The patient is a male roughly 25 years of age · this is a dermoscopic photograph of a skin lesion.
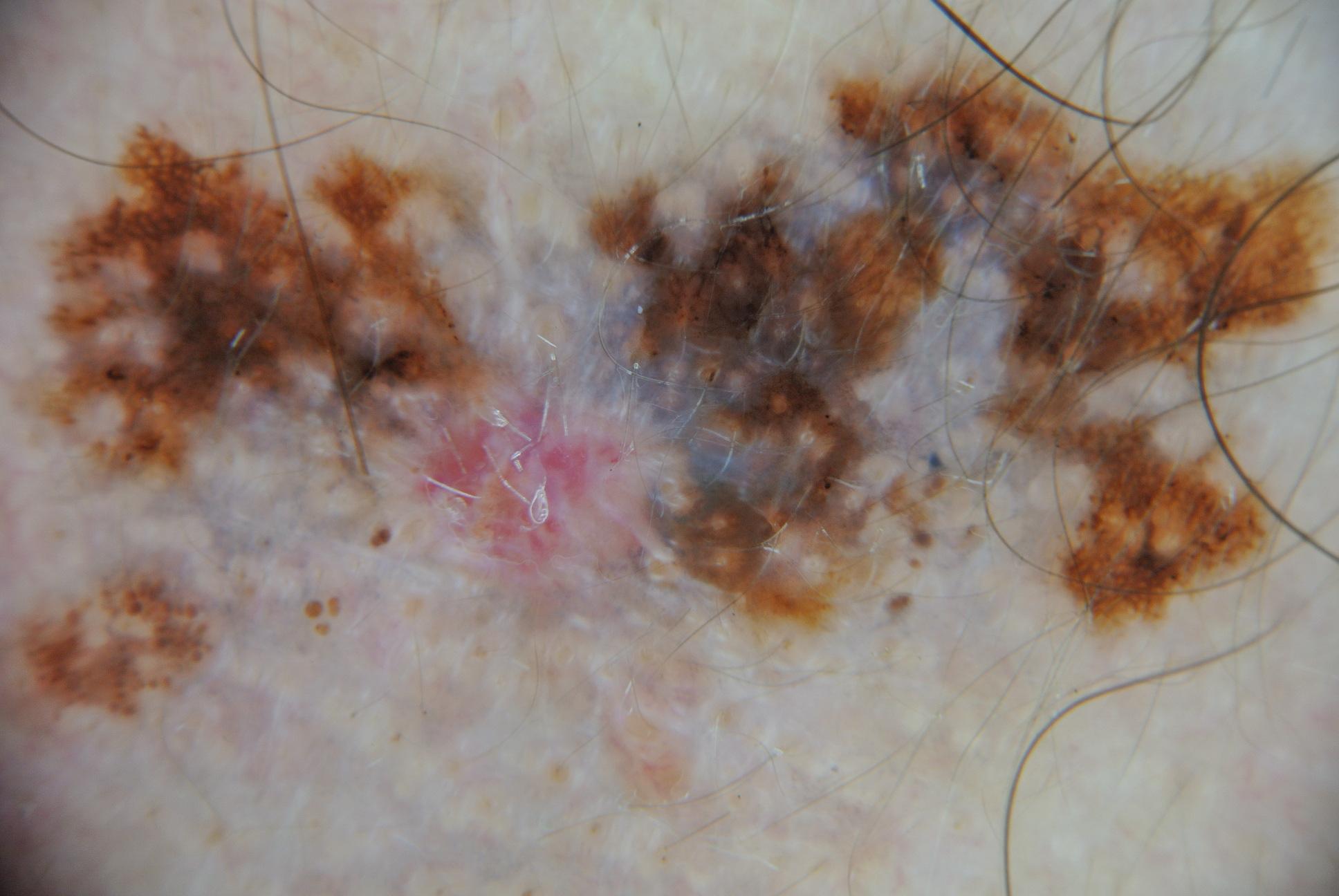| feature | finding |
|---|---|
| lesion bbox | <box>3, 52, 1337, 844</box> |
| size | large |
| dermoscopic findings | pigment network and globules |
| diagnosis | a melanoma, a malignancy |